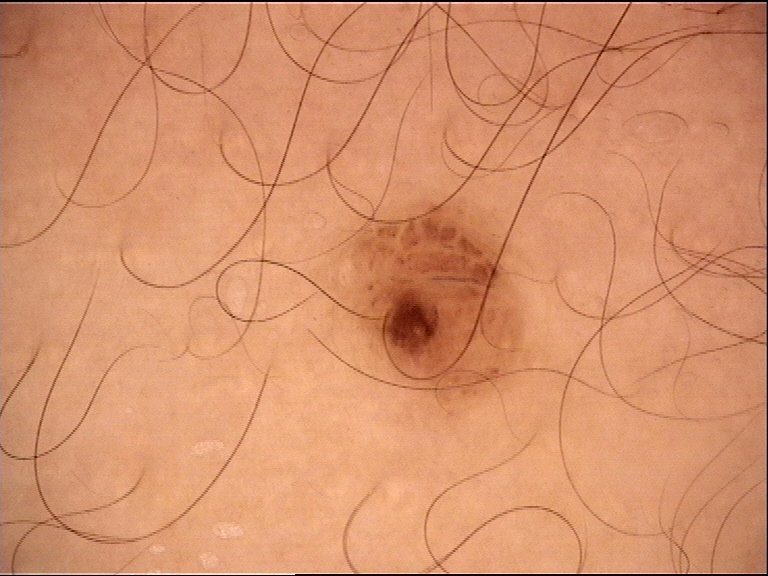A skin lesion imaged with a dermatoscope. Labeled as a dysplastic compound nevus.